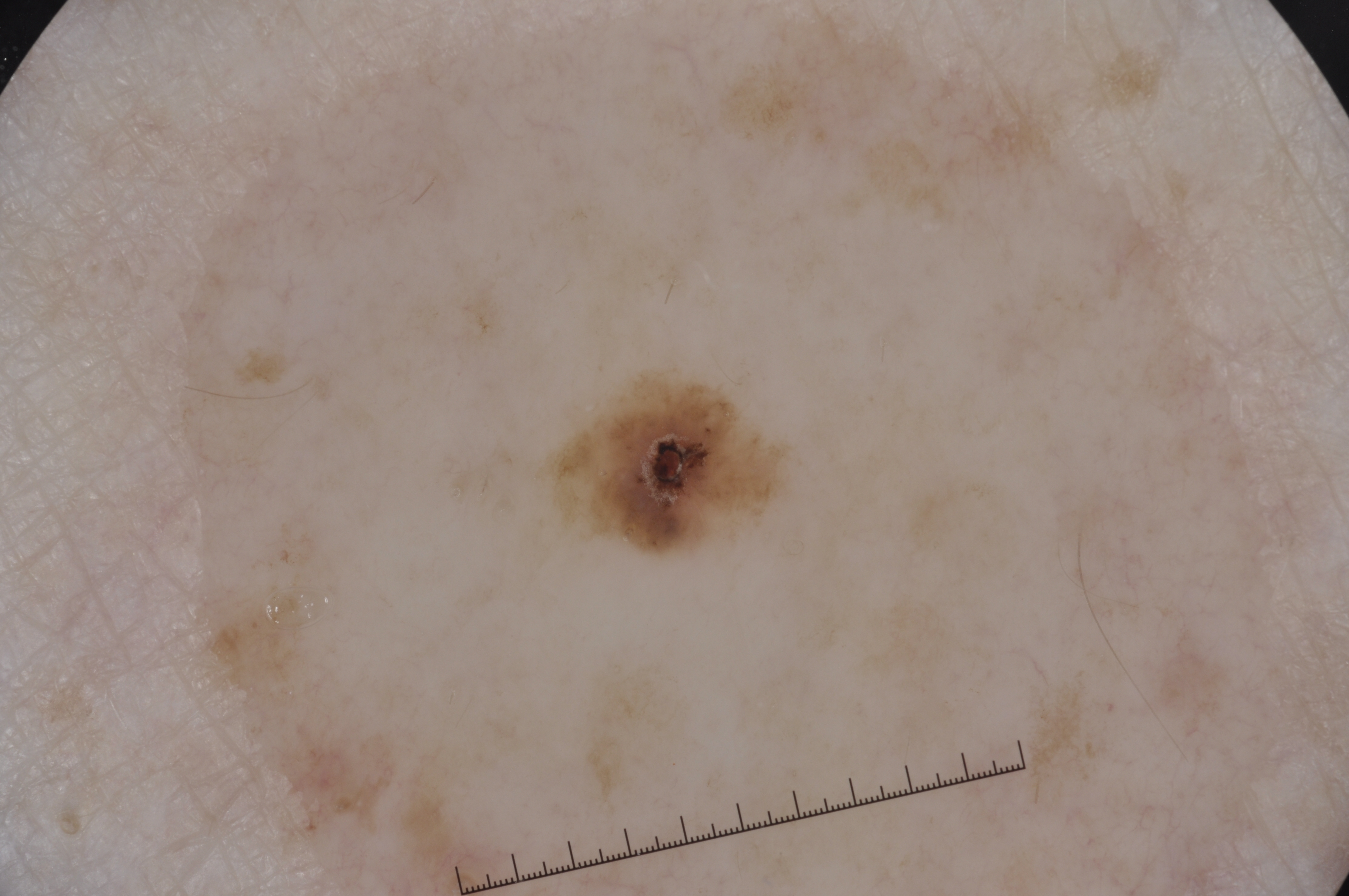modality = dermoscopic image; patient = female, aged 48 to 52; extent = ~2% of the field; dermoscopic features not present = streaks, negative network, milia-like cysts, and pigment network; location = <bbox>559, 378, 780, 553</bbox>; assessment = a melanocytic nevus.